The patient considered this skin that appeared healthy to them. The lesion involves the back of the torso and head or neck. Fitzpatrick skin type IV; non-clinician graders estimated Monk skin tone scale 4. An image taken at an angle.
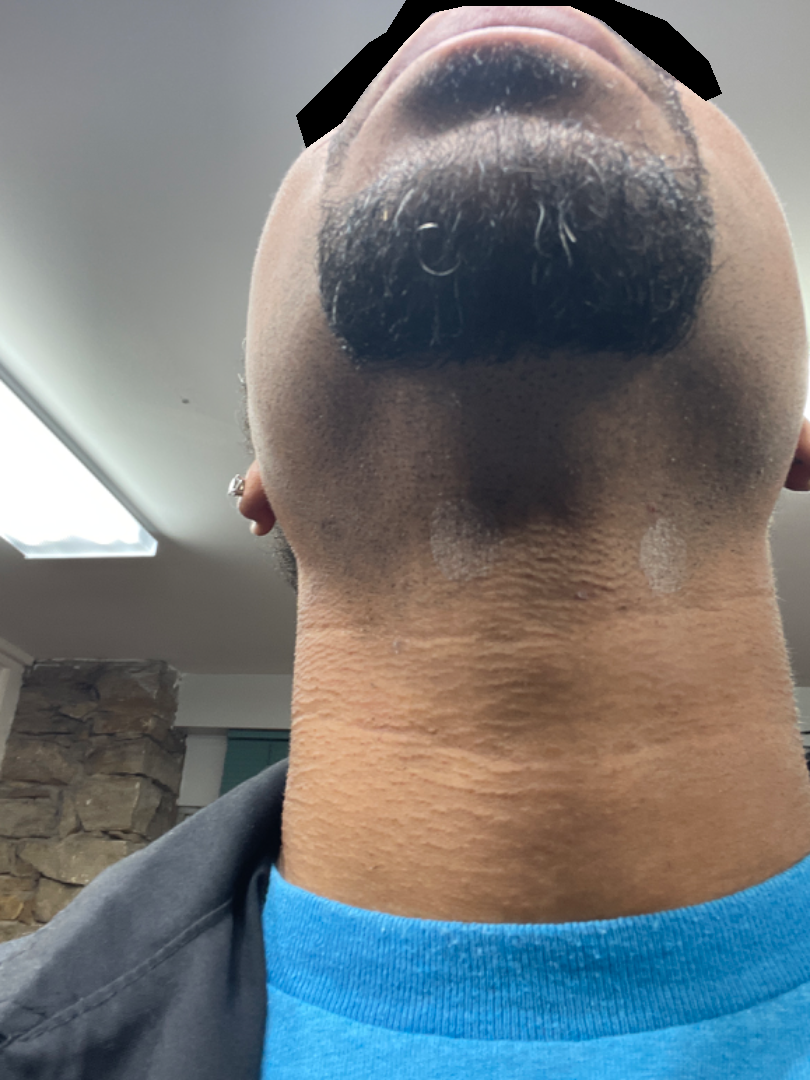Q: What was the assessment?
A: not assessable